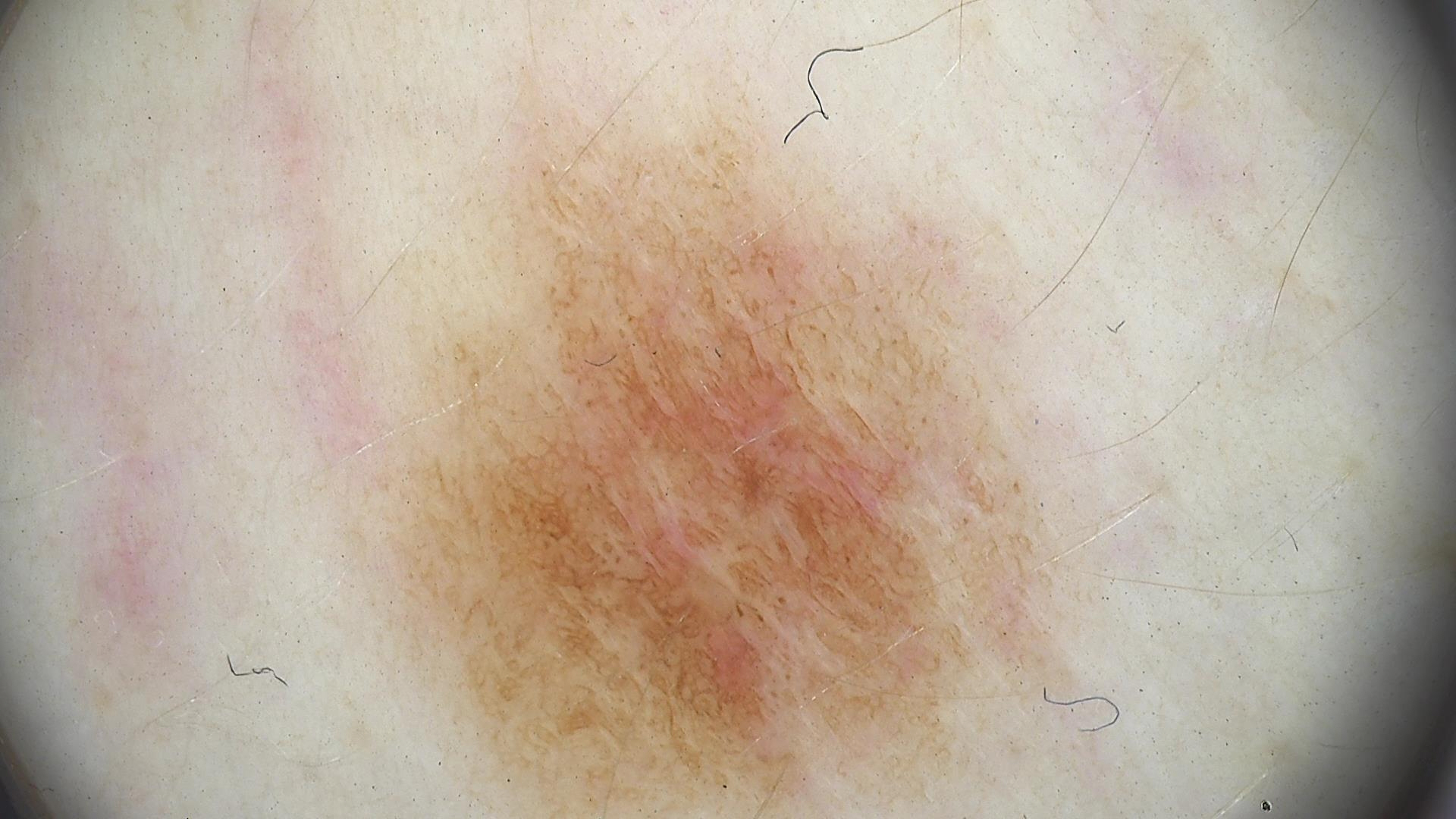The diagnostic label was a dysplastic junctional nevus.